A close-up photograph · the lesion is associated with bleeding, enlargement, itching and pain · the contributor reports associated fatigue · present for one to four weeks · female subject, age 50–59 · the patient described the issue as a rash · the contributor reports the lesion is rough or flaky, raised or bumpy and fluid-filled · the affected area is the top or side of the foot, leg, arm and back of the hand · skin tone: self-reported Fitzpatrick III.
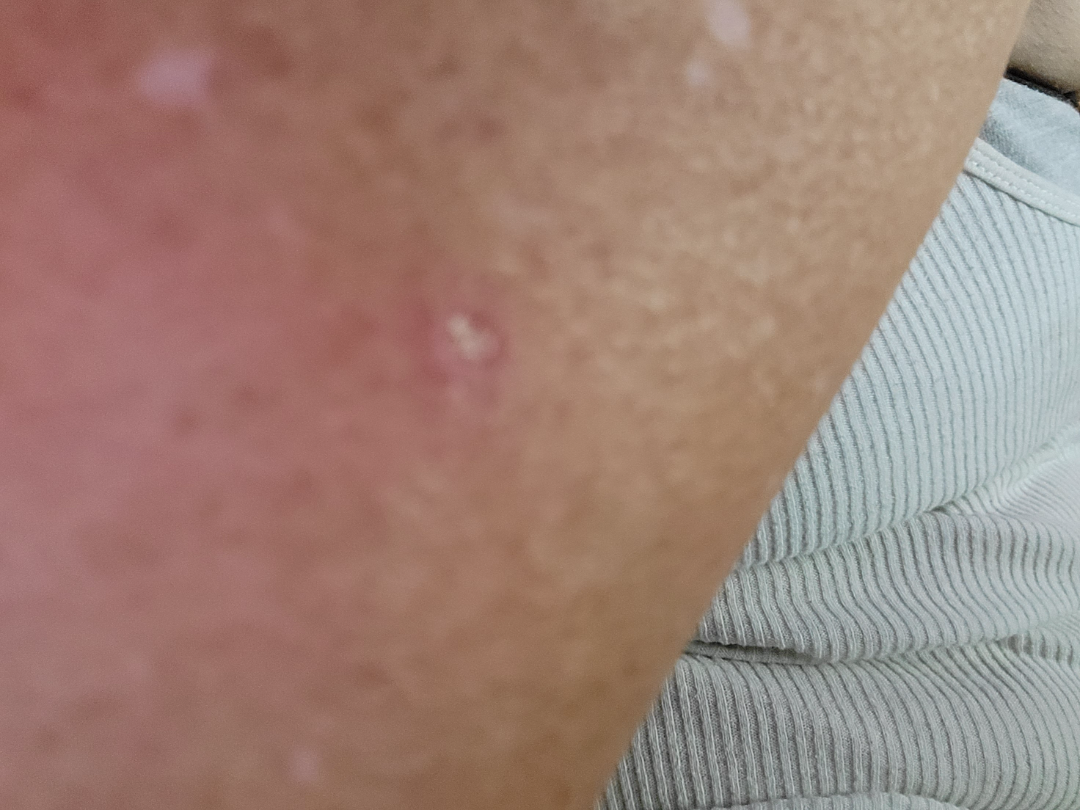The condition could not be reliably identified from the image.